The patient notes the condition has been present for about one day · the photograph is a close-up of the affected area · reported lesion symptoms include burning, bothersome appearance, darkening, pain, enlargement and itching · associated systemic symptoms include mouth sores, shortness of breath and fatigue · the affected area is the top or side of the foot, back of the hand, arm and leg · the patient described the issue as a rash · texture is reported as rough or flaky and raised or bumpy — 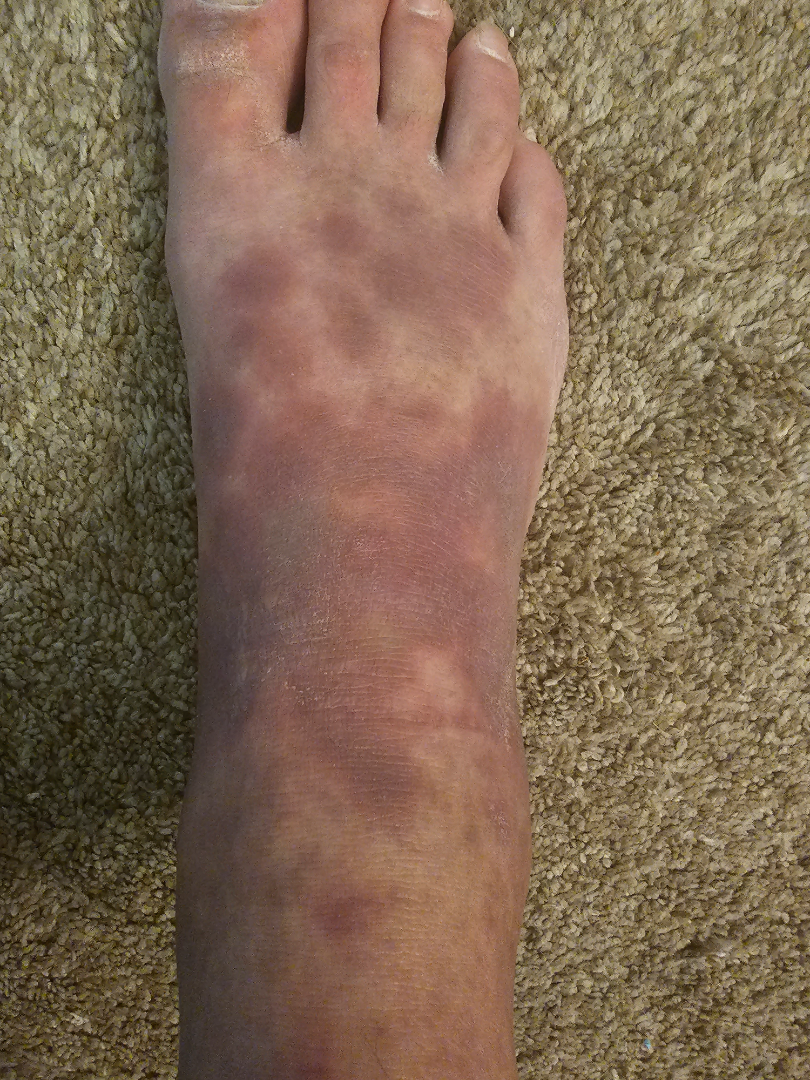assessment=the differential includes Lichen Simplex Chronicus, Eczema and Psoriasis, with no clear leading consideration; less likely is Drug Rash; less probable is Erythema multiforme; lower on the differential is Acute and chronic dermatitis; a remote consideration is Stasis Dermatitis; a more distant consideration is Lichen planus/lichenoid eruption.